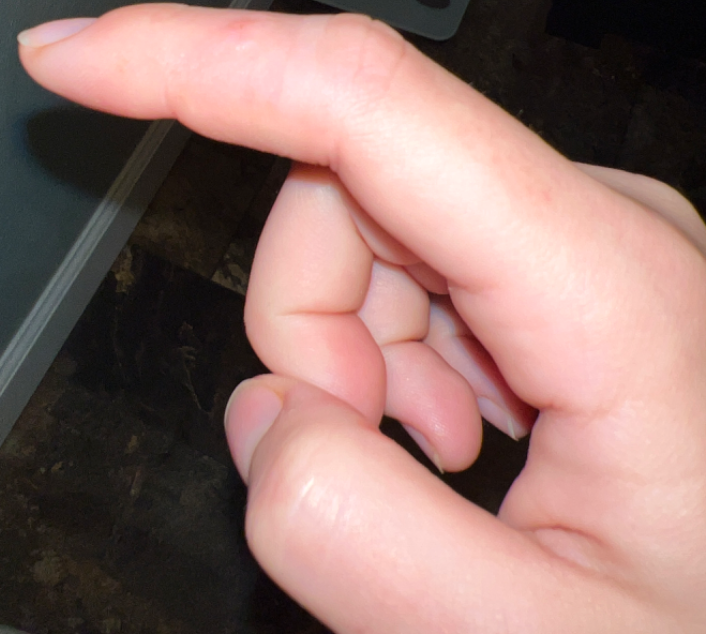Findings: The case was indeterminate on photographic review. Background: The patient considered this a rash. The lesion involves the back of the hand. The photo was captured at an angle. Reported lesion symptoms include itching, burning and enlargement. Present for less than one week. Texture is reported as fluid-filled. Female contributor, age 18–29.